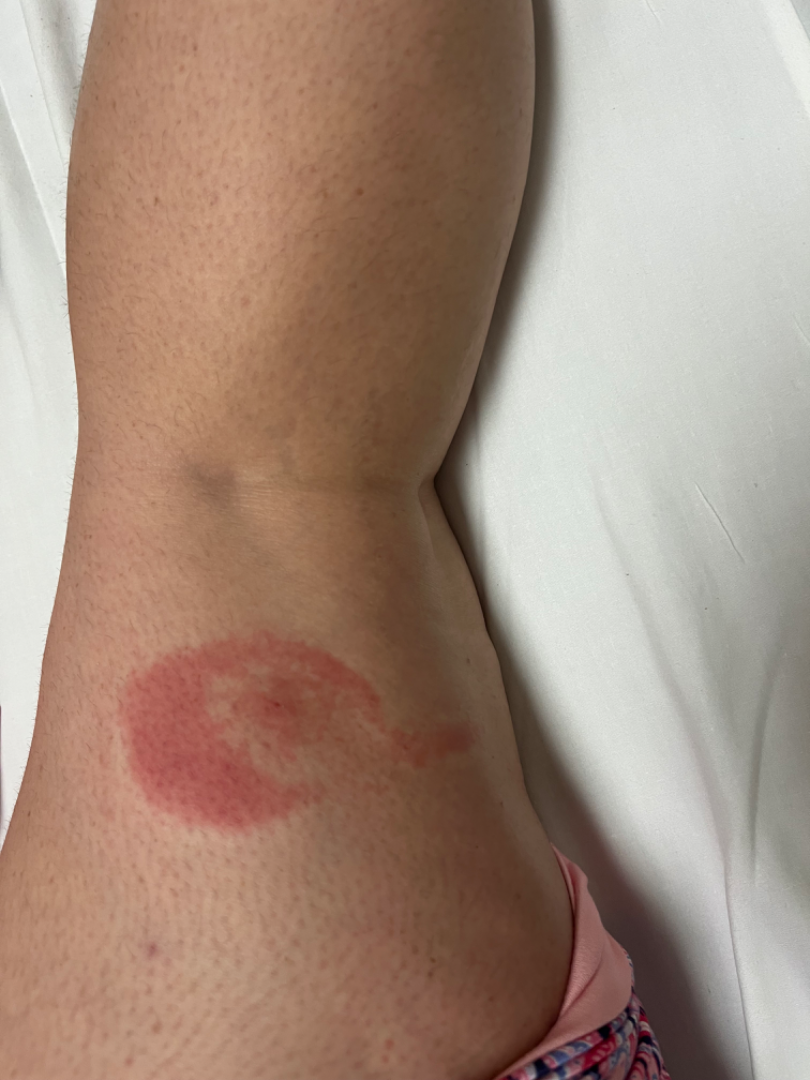skin tone = Fitzpatrick phototype IV; non-clinician graders estimated a Monk skin tone scale of 4
image framing = close-up
diagnostic considerations = single-reviewer assessment: most likely Geographic tongue; the differential also includes Insect Bite